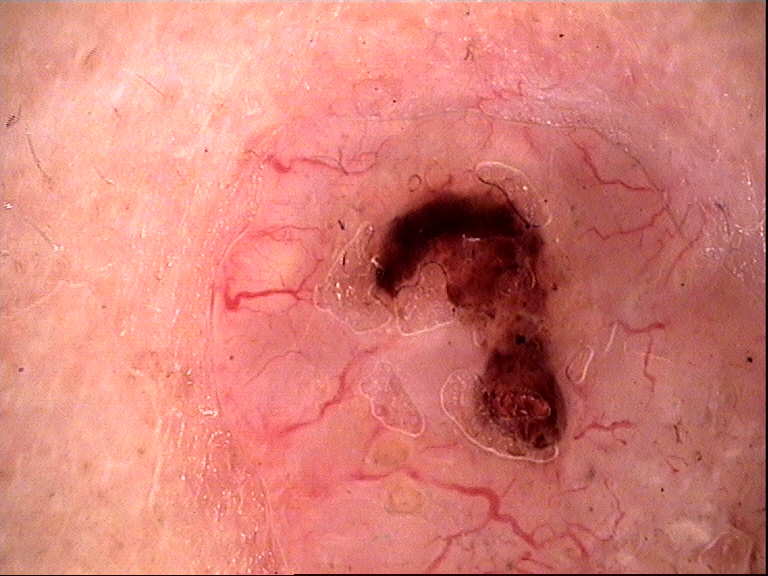modality = dermoscopy; classification = keratinocytic; class = basal cell carcinoma (biopsy-proven).